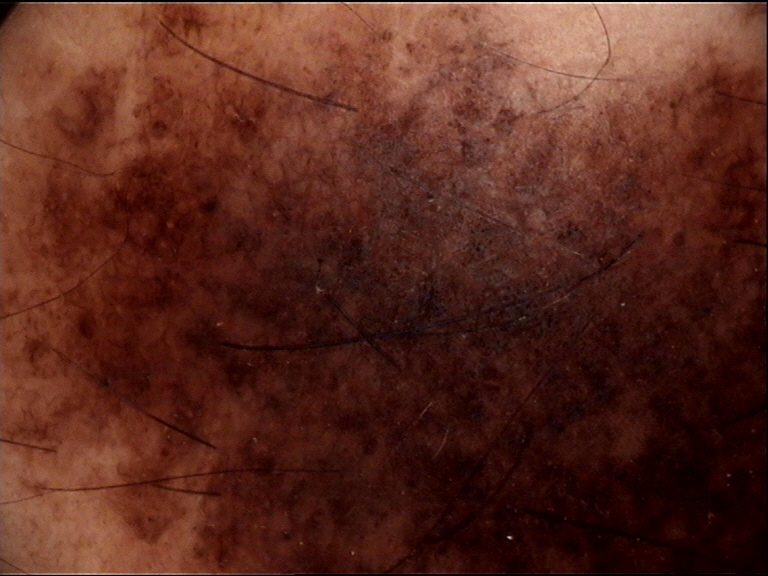Classified as a congenital compound nevus.